The sole of the foot and top or side of the foot are involved; an image taken at an angle; the subject is female.
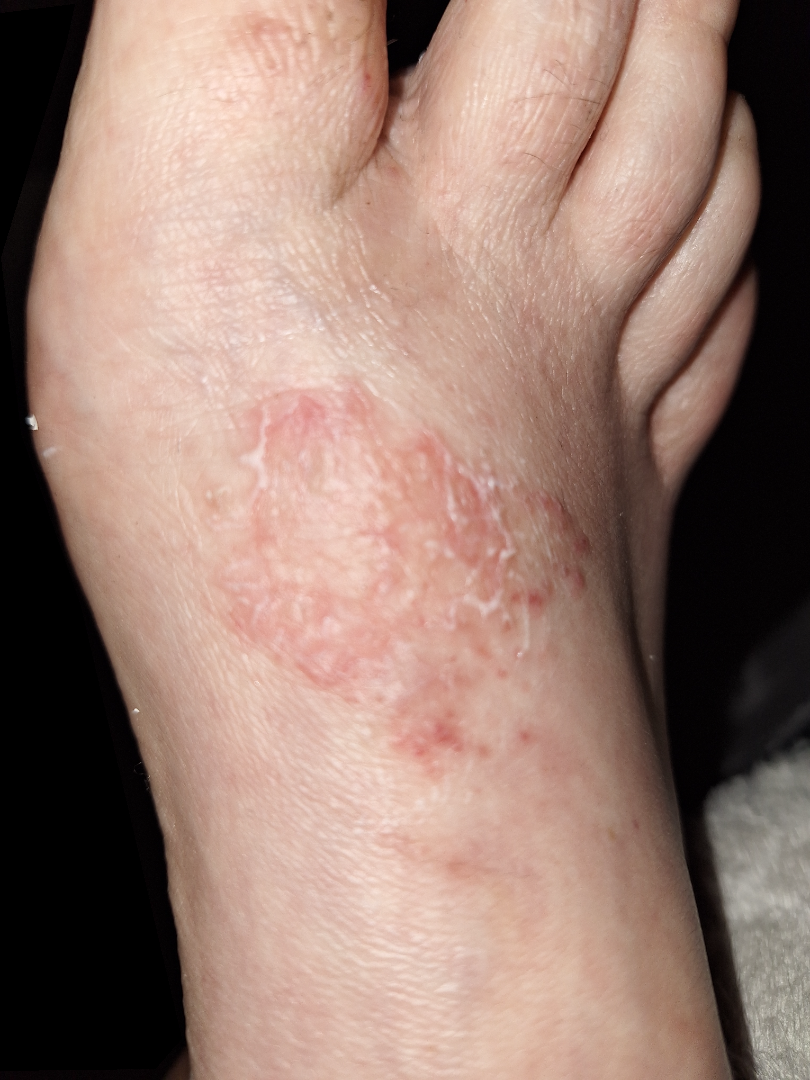Findings: The reviewing dermatologist's impression was: most likely Tinea.